A clinical photograph showing a skin lesion. A male patient aged 59. History notes pesticide exposure, prior malignancy (patient or family), and alcohol use. The patient is Fitzpatrick II — 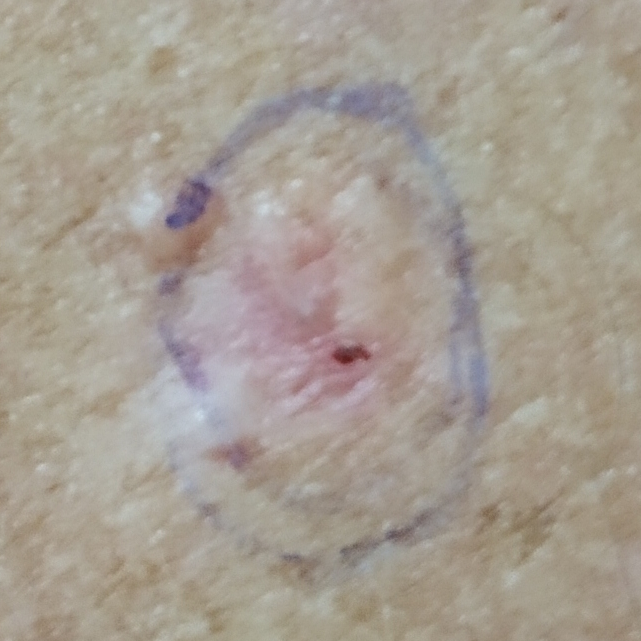Clinical context:
The lesion involves the back. Measuring about 1 × 1 mm. The patient describes that the lesion hurts, itches, and has bled, but is not elevated.
Conclusion:
Histopathology confirmed a basal cell carcinoma.